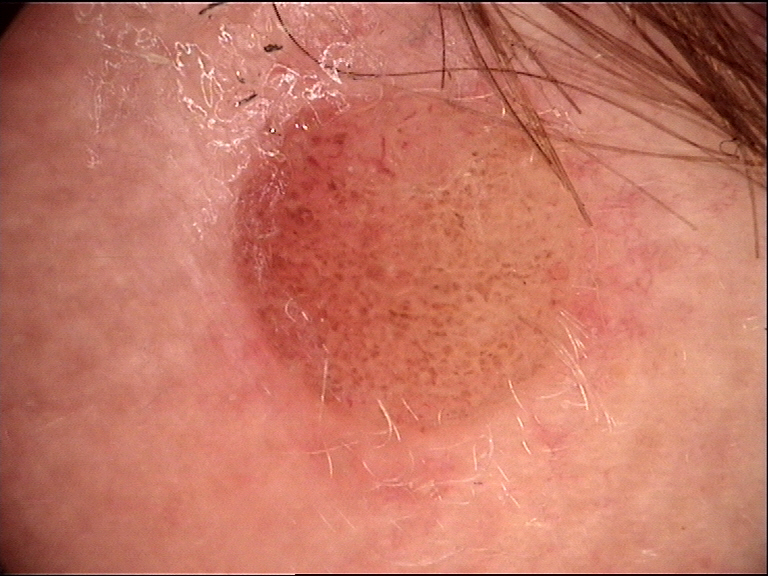A dermoscopic close-up of a skin lesion. This is a banal lesion. The diagnostic label was a dermal nevus.